The affected area is the arm · male patient, age 60–69 · the photo was captured at an angle — 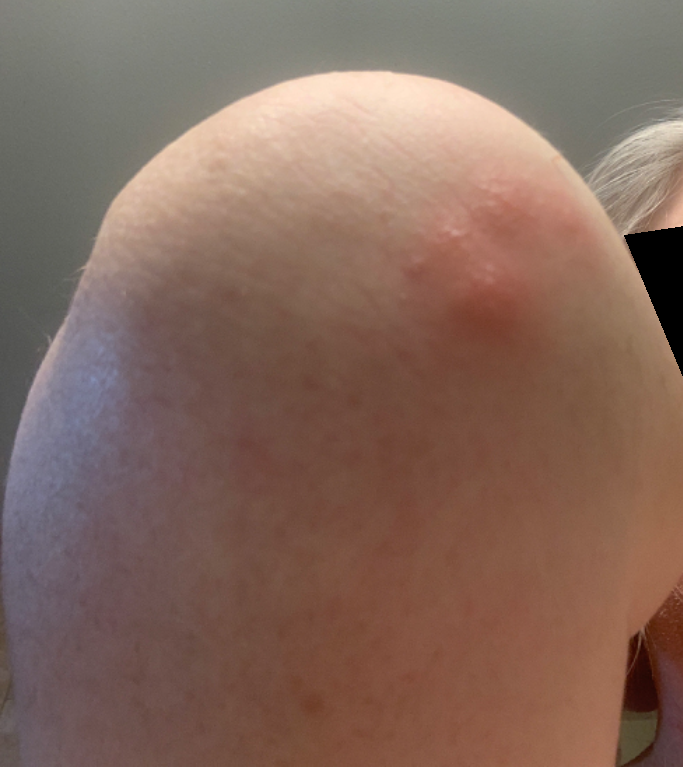assessment — indeterminate from the photograph